The subject is a male aged 18–29; the patient reports the condition has been present for more than one year; the patient reports the lesion is flat; the patient reports bothersome appearance and enlargement; the patient considered this a rash; this image was taken at a distance; the back of the torso, arm and leg are involved: 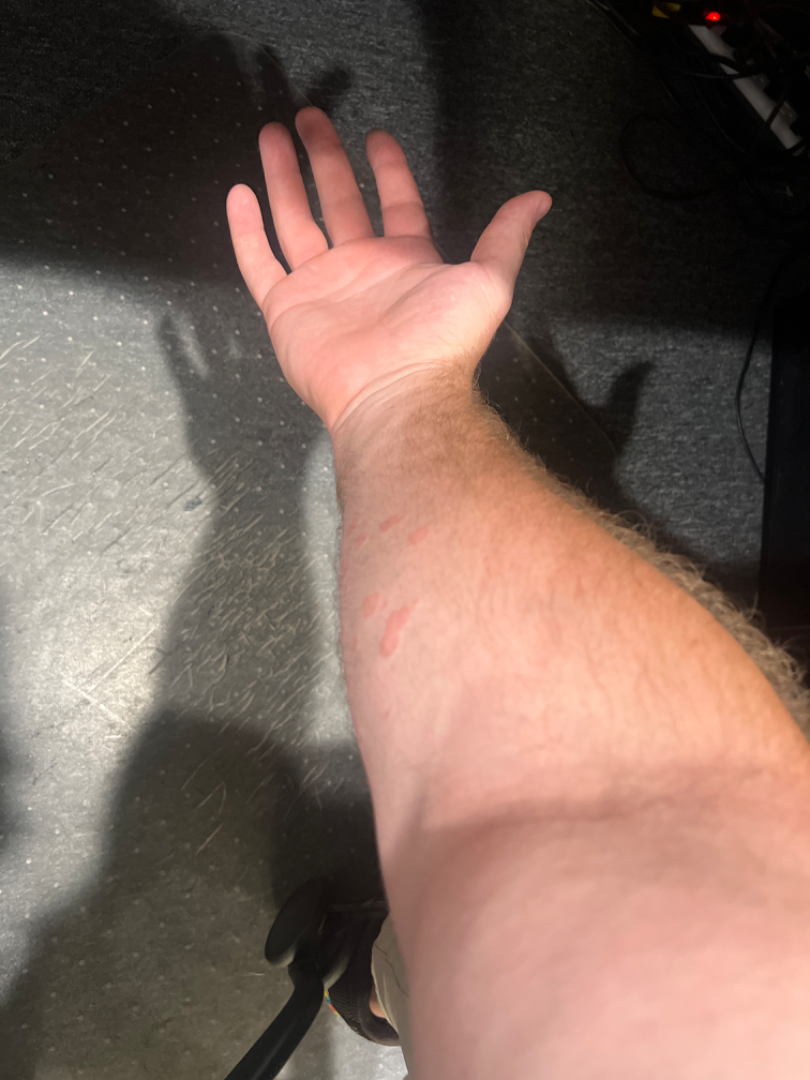The reviewing dermatologist was unable to assign a differential diagnosis from the image.